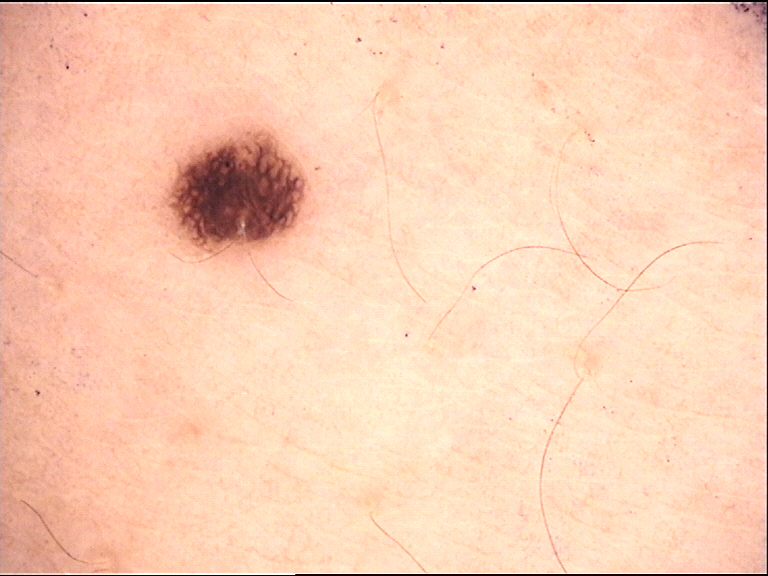Findings:
- label — dysplastic junctional nevus (expert consensus)